The contributor is a male aged 30–39; the photograph is a close-up of the affected area; the contributor reports the condition has been present for less than one week; no relevant lesion symptoms reported; the affected area is the back of the hand; the patient considered this a rash; the contributor reports the lesion is raised or bumpy:
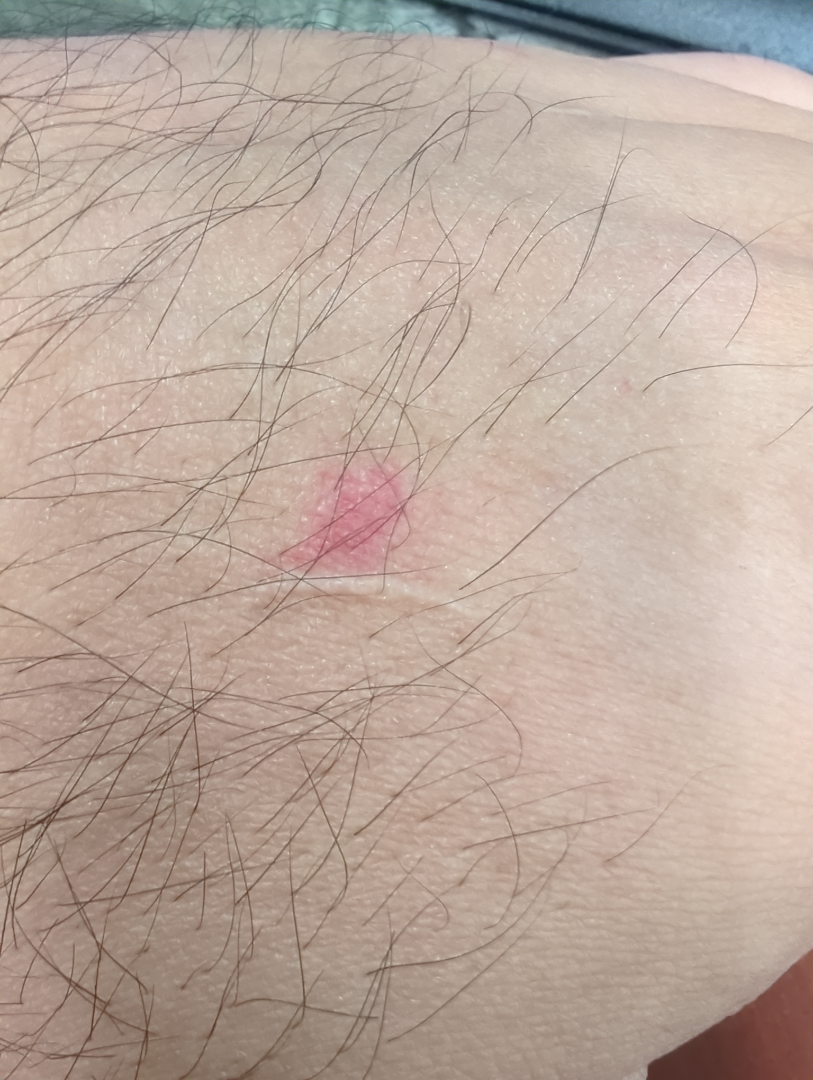  assessment: not assessable